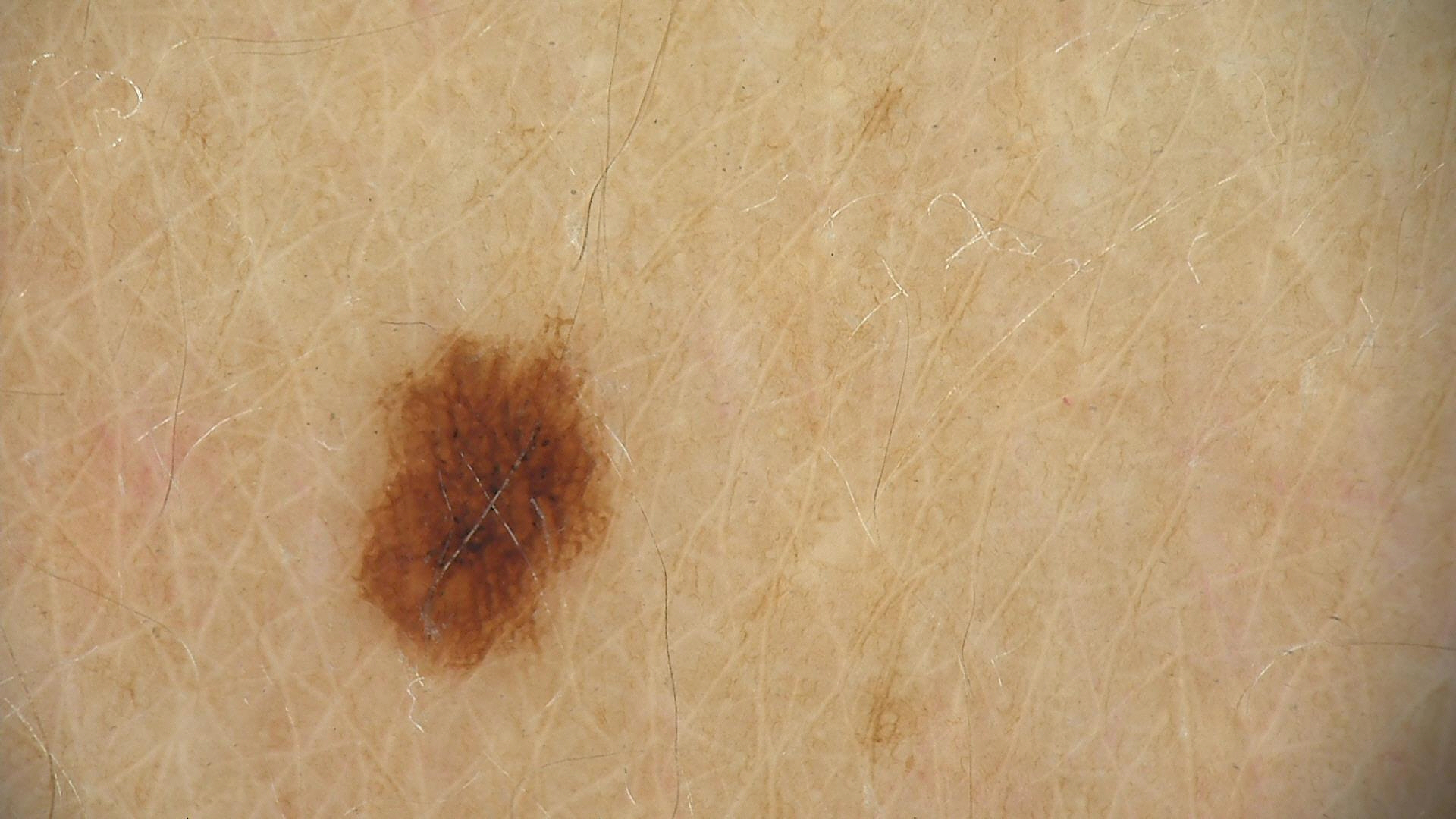A dermoscopic close-up of a skin lesion. Labeled as a benign lesion — a dysplastic junctional nevus.